Dermoscopy of a skin lesion: 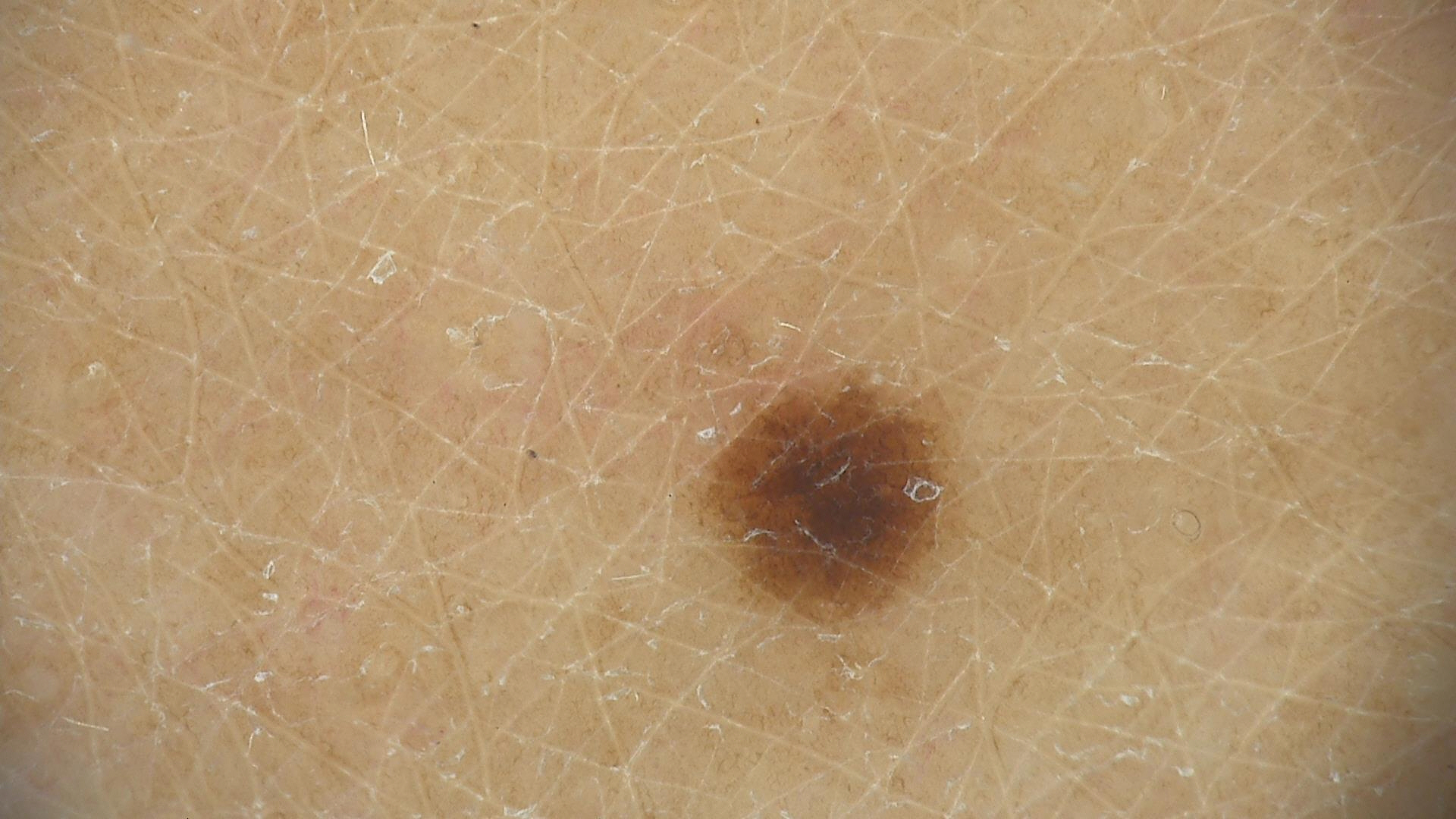Conclusion: Diagnosed as a banal lesion — a junctional nevus.